A clinical close-up photograph of a skin lesion · recorded as Fitzpatrick III · a female patient 46 years old · history notes alcohol use.
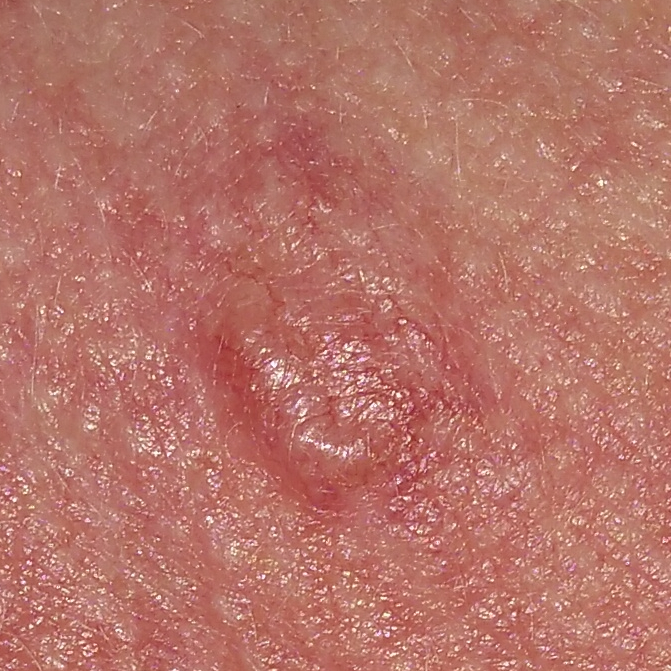| key | value |
|---|---|
| site | the neck |
| lesion size | 12x6 mm |
| symptoms | elevation / no itching |
| pathology | basal cell carcinoma (biopsy-proven) |